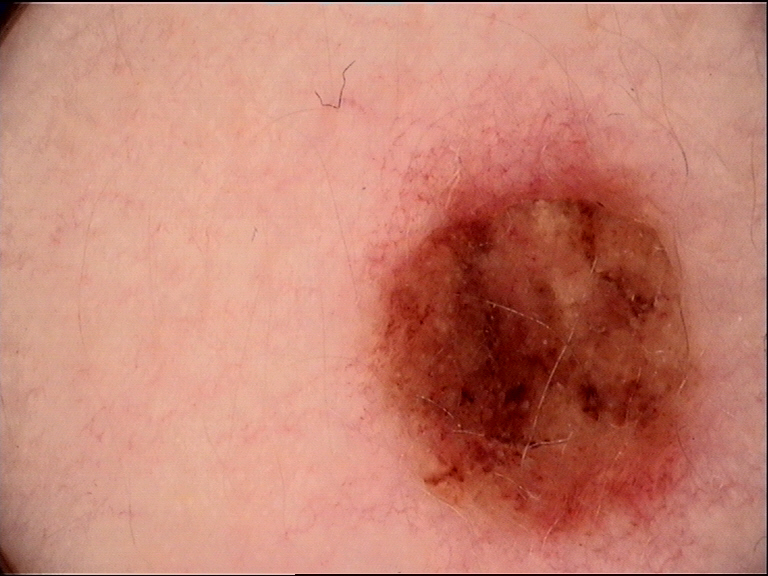Findings:
• modality — dermoscopy
• diagnostic label — dysplastic compound nevus (expert consensus)